A dermatoscopic image of a skin lesion. The patient says their skin reddens painfully with sun exposure. A male patient age 89 — 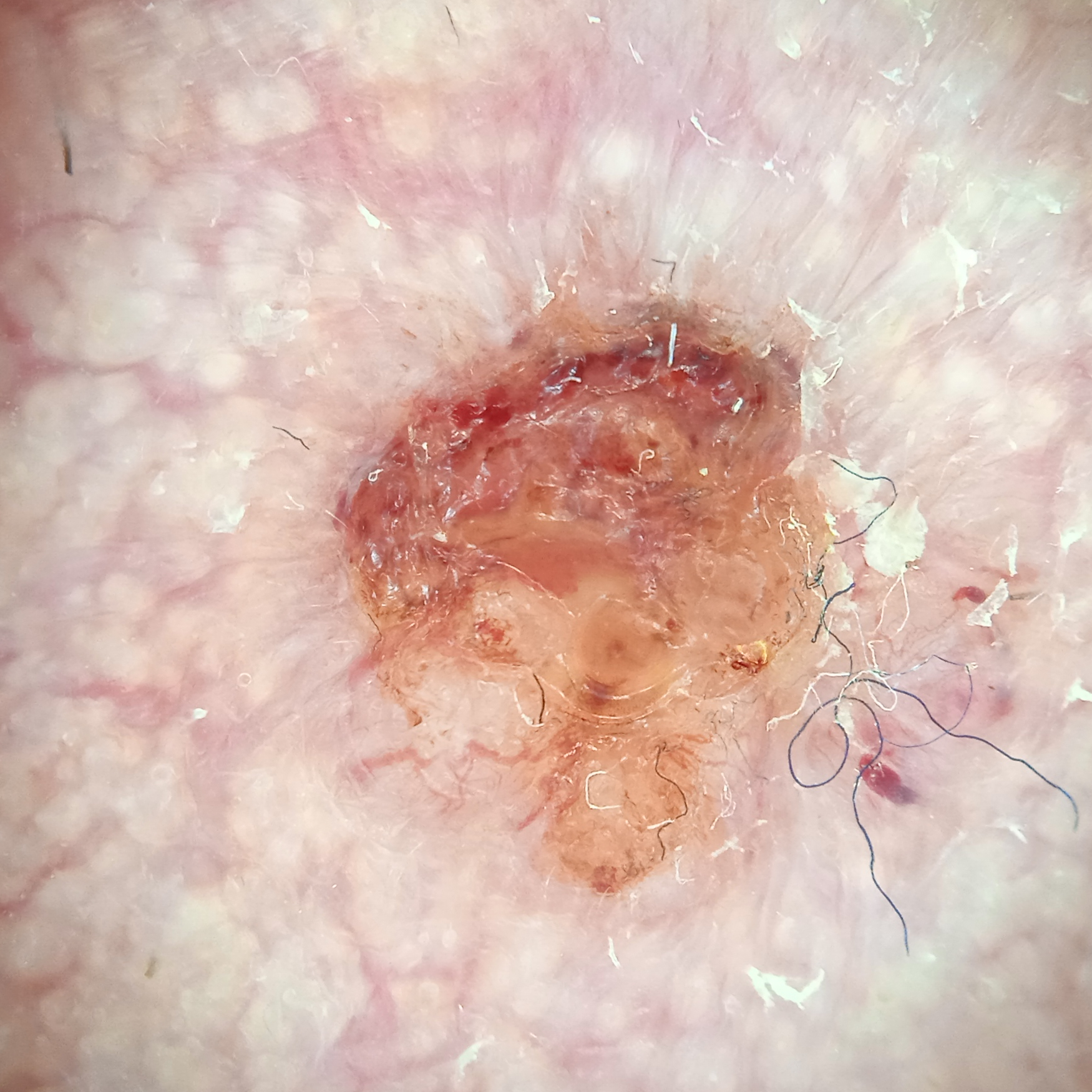Located on the face.
The lesion measures approximately 8.5 mm.
On biopsy, the diagnosis was a basal cell carcinoma, following excision, with a measured tumor thickness of 2.2 mm.